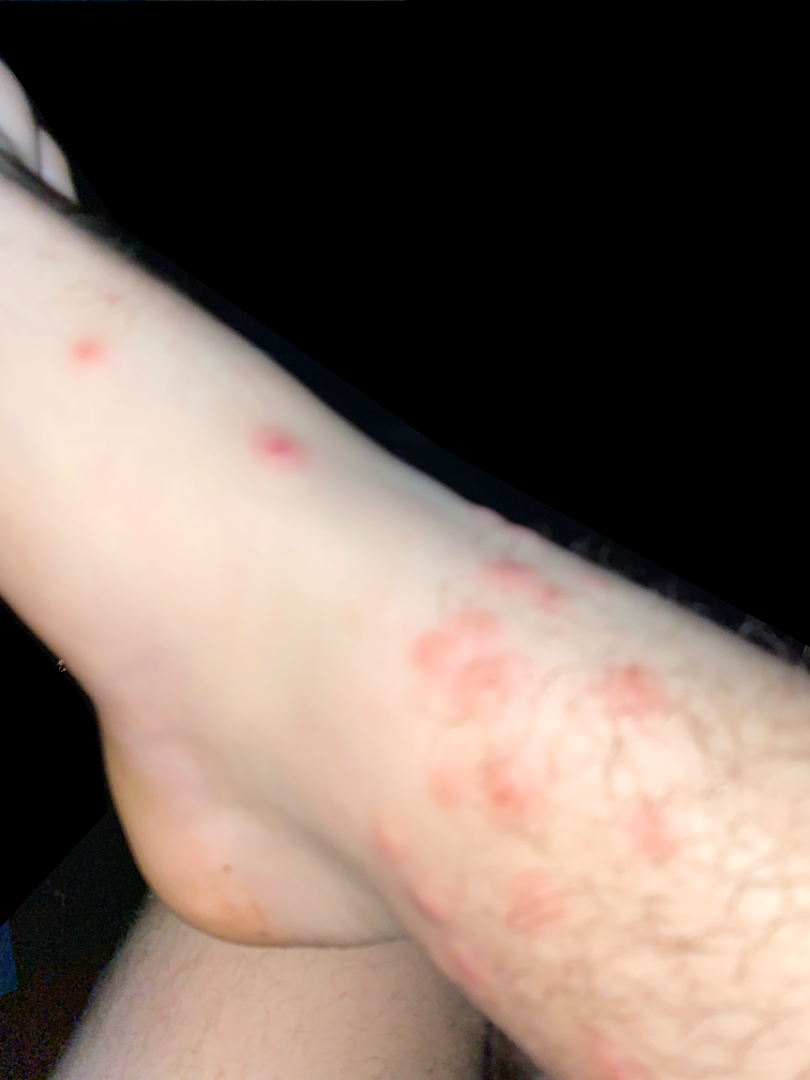Findings: The image was not sufficient for the reviewer to characterize the skin condition.